A dermoscopy image of a single skin lesion:
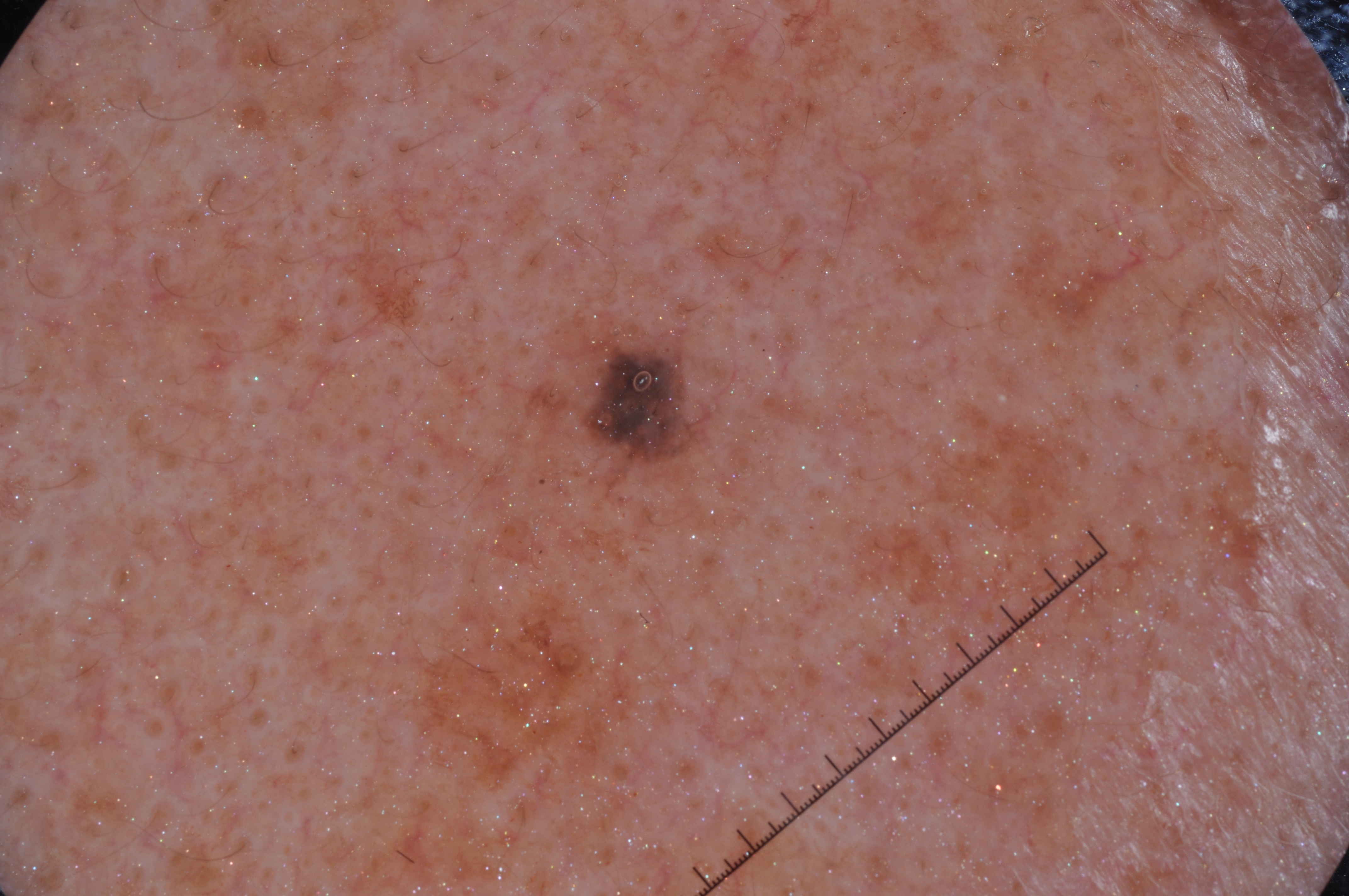The dermoscopic pattern shows no milia-like cysts, pigment network, streaks, or negative network. The lesion is small relative to the field of view. The lesion's extent is x1=581 y1=346 x2=699 y2=465. Diagnosed as a melanocytic nevus.